A dermoscopy image of a single skin lesion.
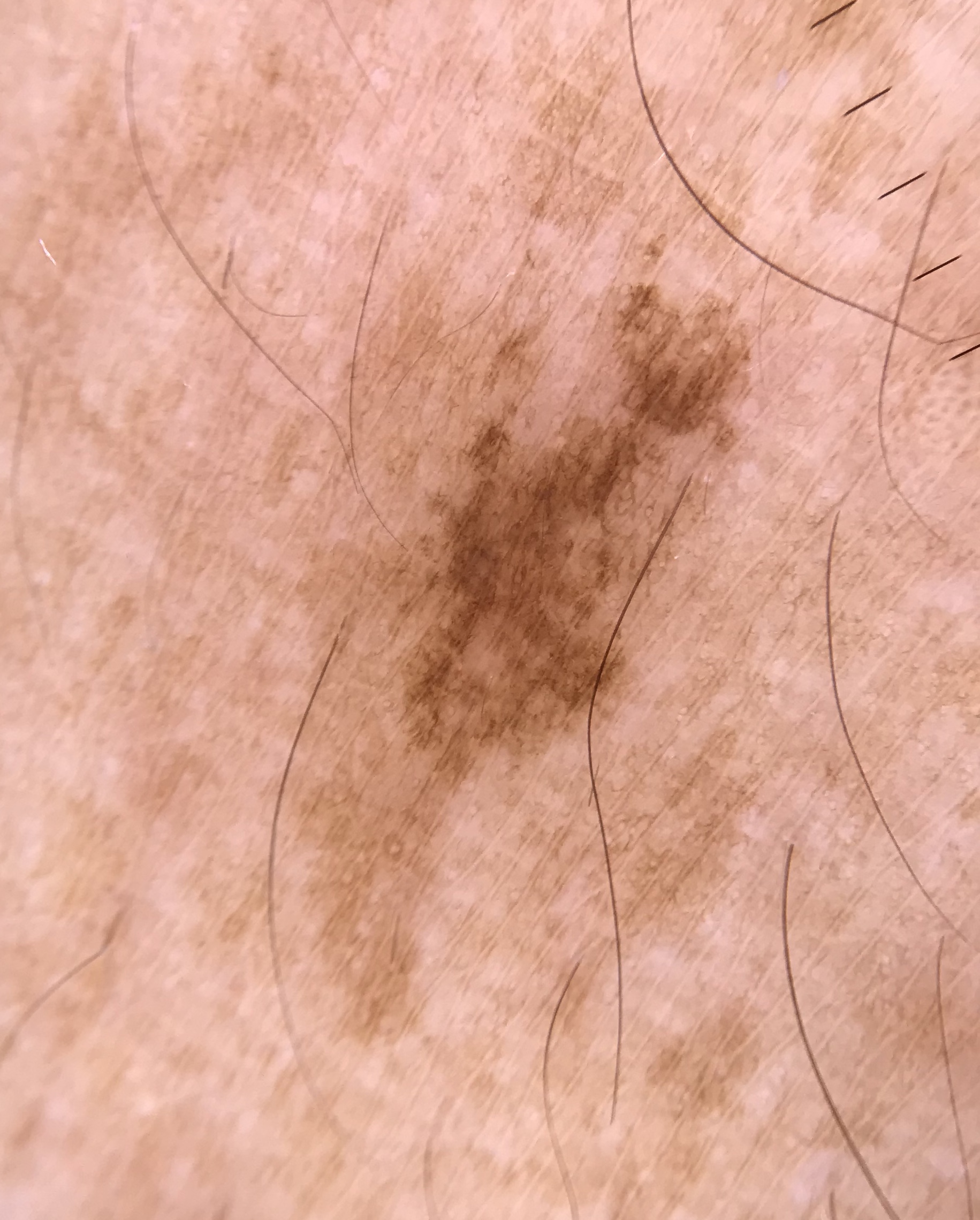{
  "diagnosis": {
    "name": "solar lentigo",
    "code": "sl",
    "malignancy": "benign",
    "super_class": "melanocytic",
    "confirmation": "expert consensus"
  }
}